A clinical close-up photograph of a skin lesion · a female subject aged 73.
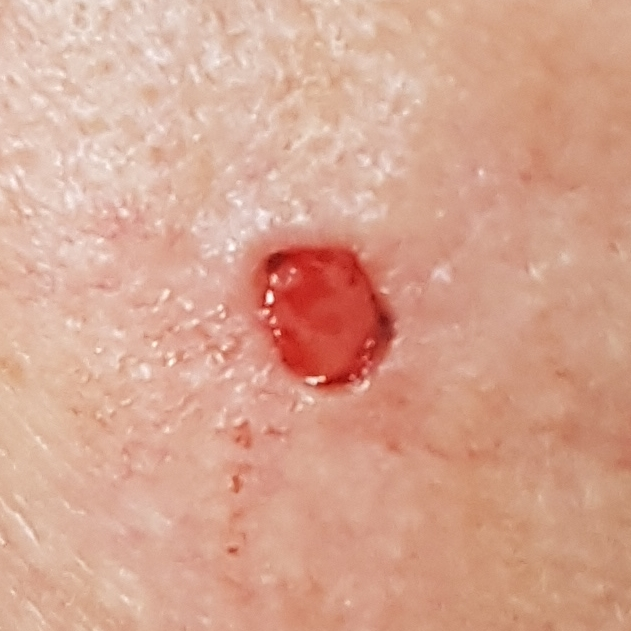Q: What is the anatomic site?
A: the face
Q: Lesion size?
A: approx. 7 × 6 mm
Q: What symptoms does the patient report?
A: bleeding, pain, growth, itching
Q: What is the diagnosis?
A: basal cell carcinoma (biopsy-proven)